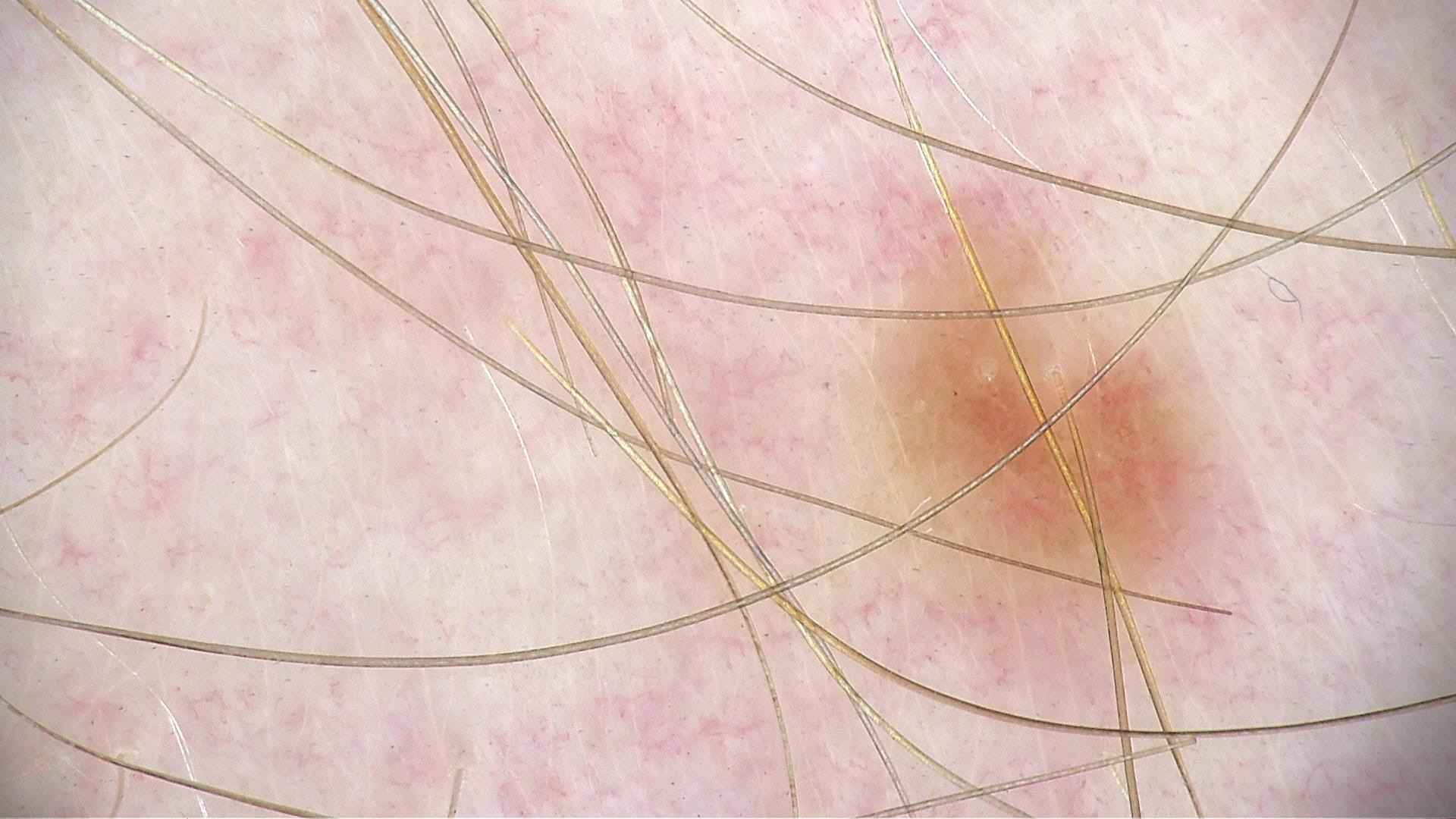Q: What is the diagnosis?
A: dysplastic junctional nevus (expert consensus)